Close-up view — 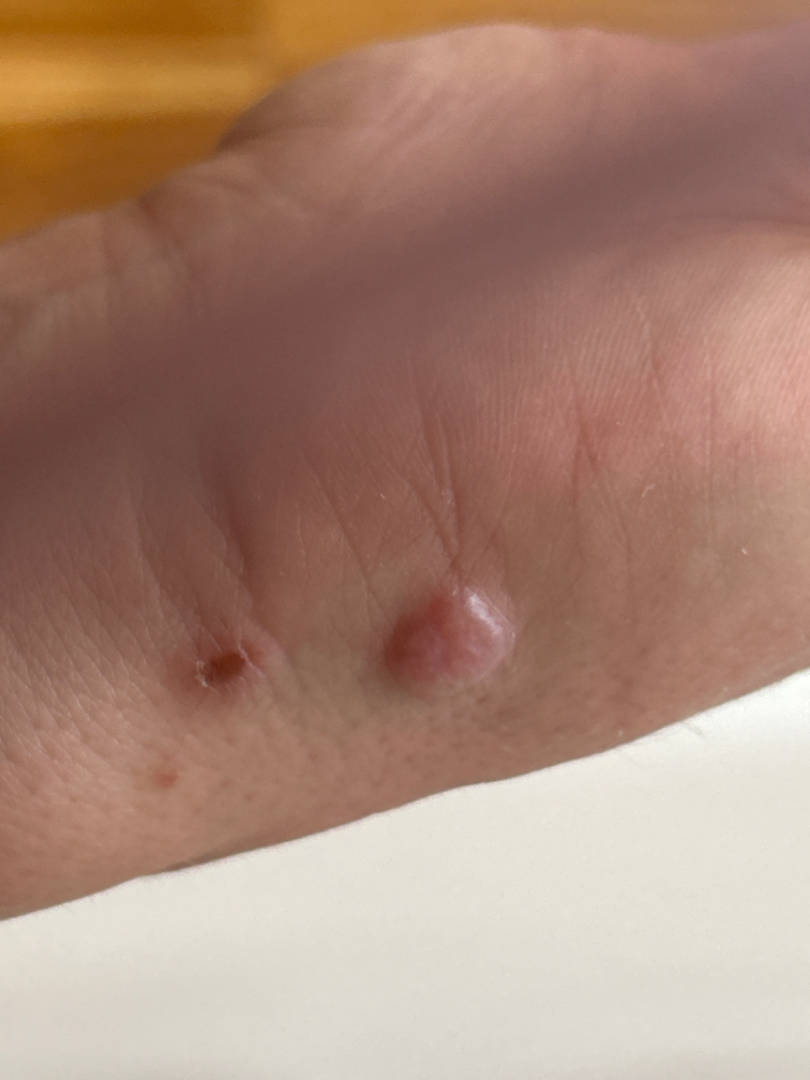<report>
<patient_category>skin that appeared healthy to them</patient_category>
<symptoms>itching</symptoms>
<differential>
  <tied_lead>Lichen planus/lichenoid eruption, Molluscum Contagiosum</tied_lead>
</differential>
</report>